The chart documents a prior melanoma. A female patient in their mid- to late 50s — 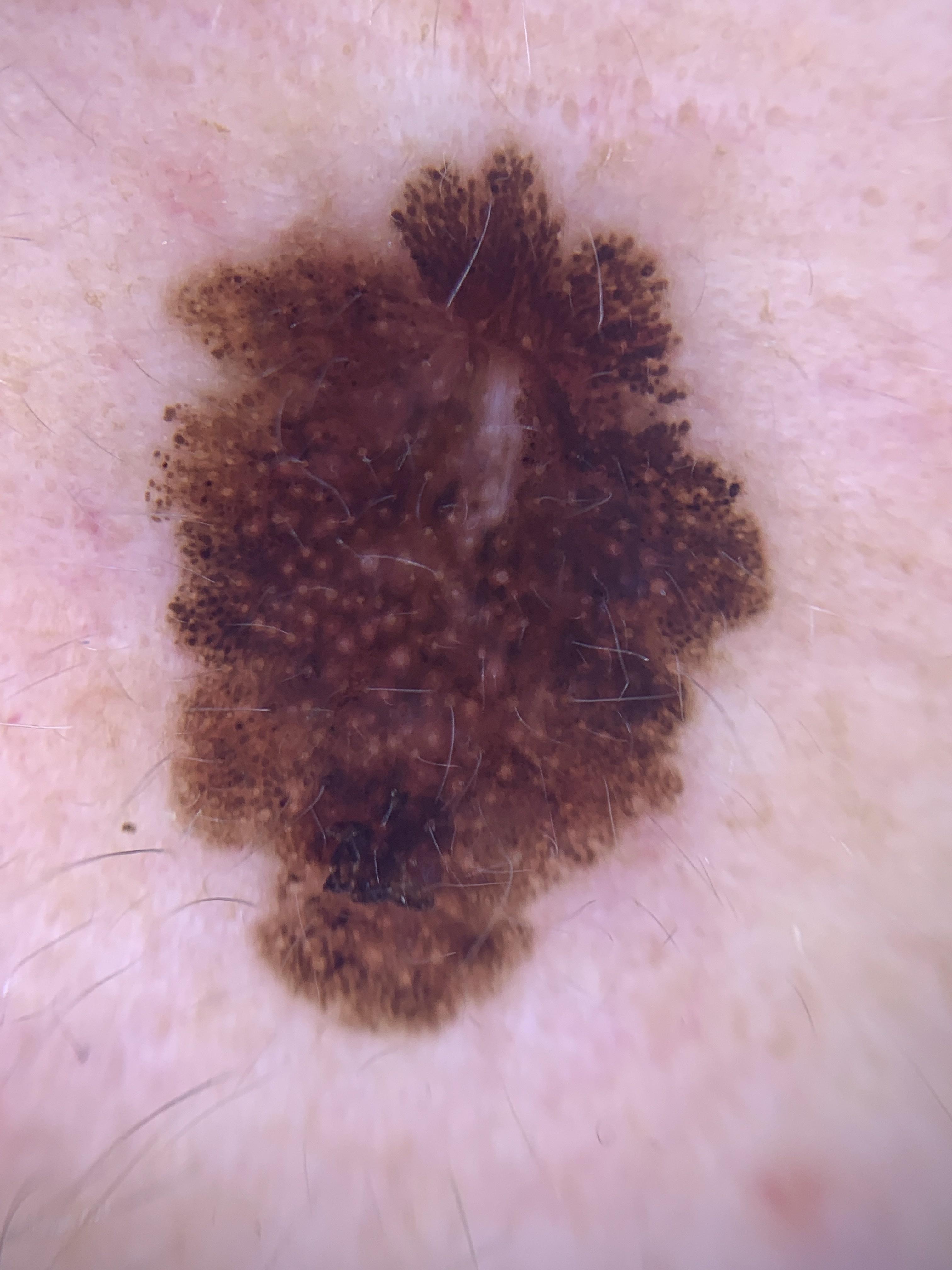<lesion>
<diagnosis>
<name>Melanoma</name>
<malignancy>malignant</malignancy>
<confirmation>histopathology</confirmation>
</diagnosis>
</lesion>